The photo was captured at a distance · the lesion involves the front of the torso.
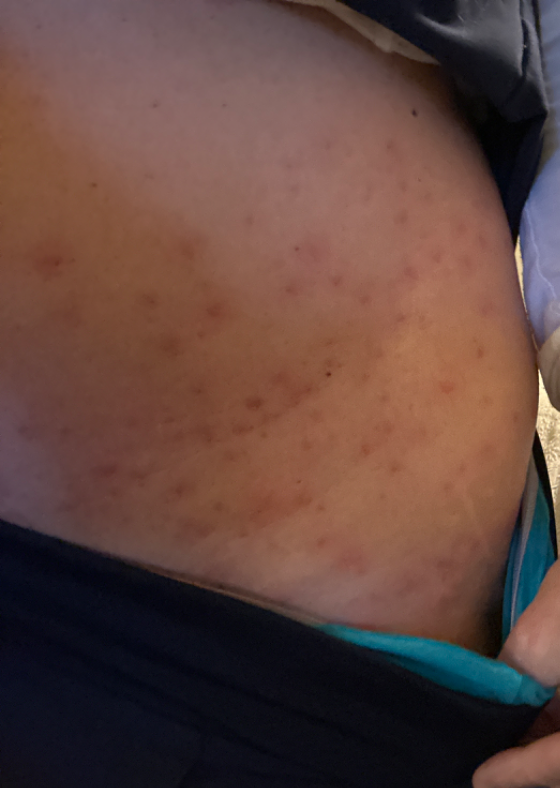Impression:
On photographic review: Scabies (considered); Folliculitis (considered); Insect Bite (considered).